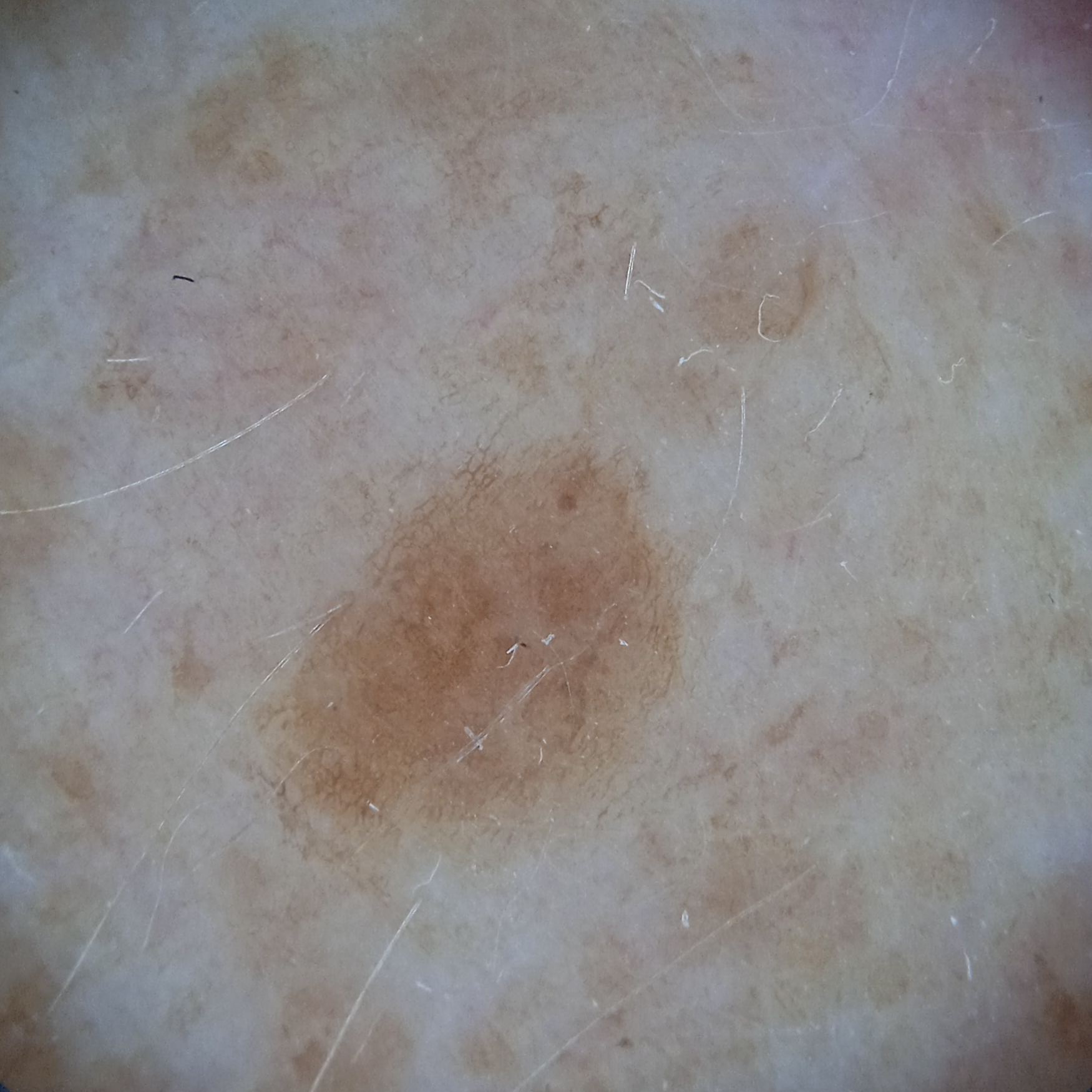Case:
– subject · female, 78 years of age
– referral context · research study (no referral diagnosis)
– imaging · dermoscopic image
– site · an arm
– diagnostic label · seborrheic keratosis (dermatologist consensus)